A female subject, about 45 years old. A dermoscopy image of a single skin lesion:
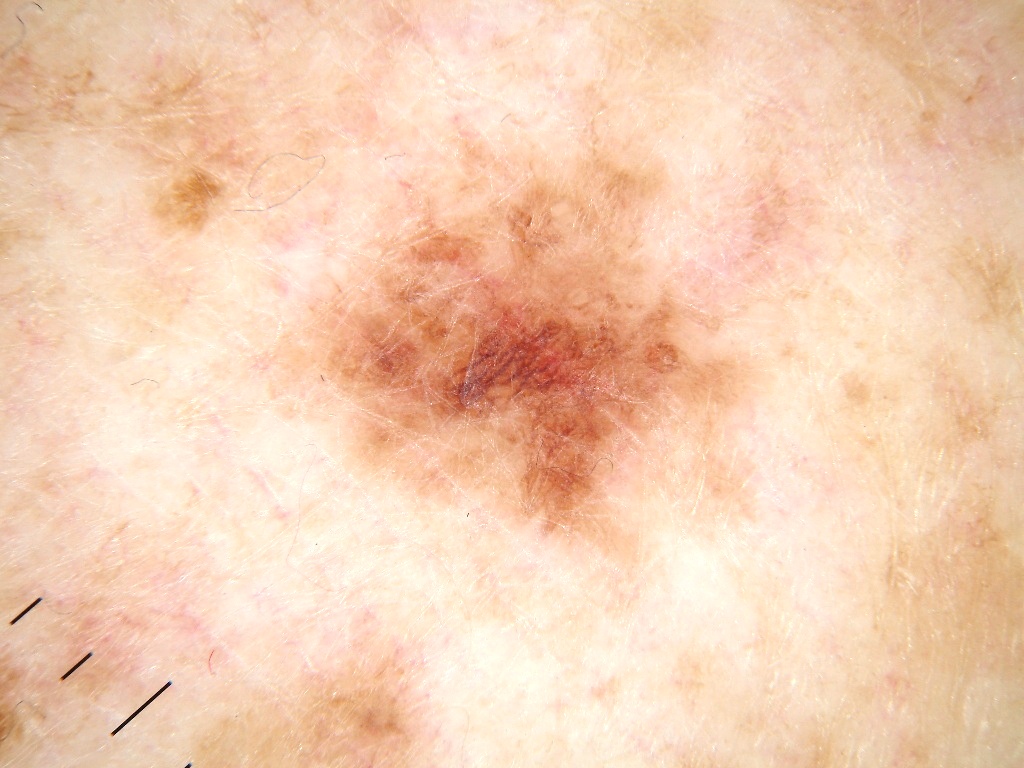Q: How much of the field does the lesion occupy?
A: moderate
Q: What does dermoscopy show?
A: pigment network
Q: Where is the lesion located?
A: x1=266, y1=138, x2=753, y2=589
Q: What is this lesion?
A: a melanocytic nevus